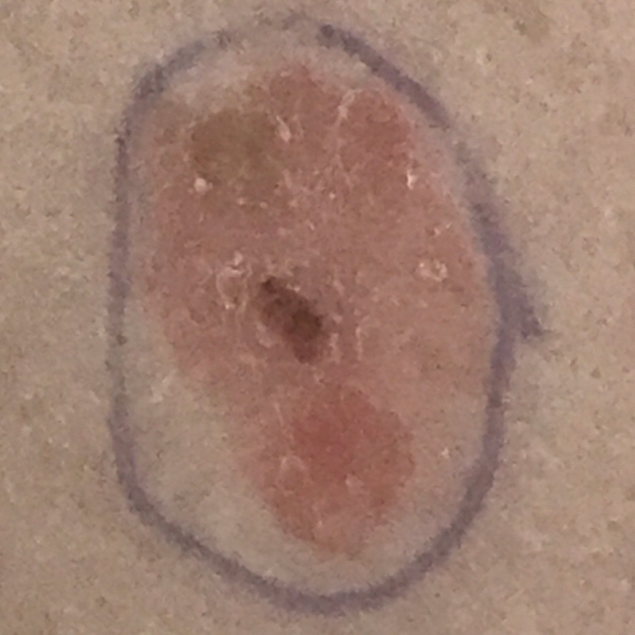  image: clinical photograph
  risk_factors:
    positive:
      - prior cancer (patient or family)
      - prior skin cancer (patient or family)
    negative:
      - smoking
  lesion_location: the back
  lesion_size:
    diameter_1_mm: 16.0
    diameter_2_mm: 11.0
  symptoms:
    absent:
      - elevation
      - itching
  diagnosis:
    name: squamous cell carcinoma
    code: SCC
    malignancy: malignant
    confirmation: histopathology